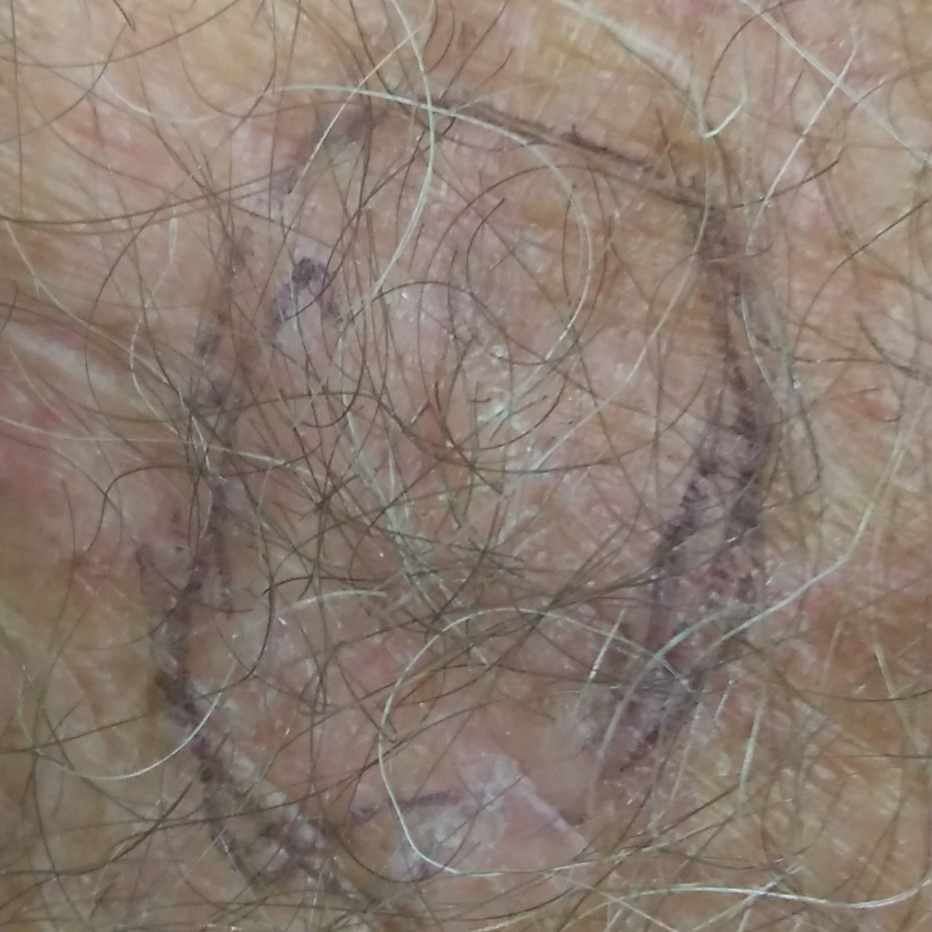modality — clinical photo | subject — male, age 82 | exposures — no prior skin cancer (patient or family), no prior malignancy (patient or family) | skin type — II | site — a forearm | lesion diameter — 6x6 mm | symptoms — itching | pathology — actinic keratosis (biopsy-proven).